A dermoscopic photograph of a skin lesion: 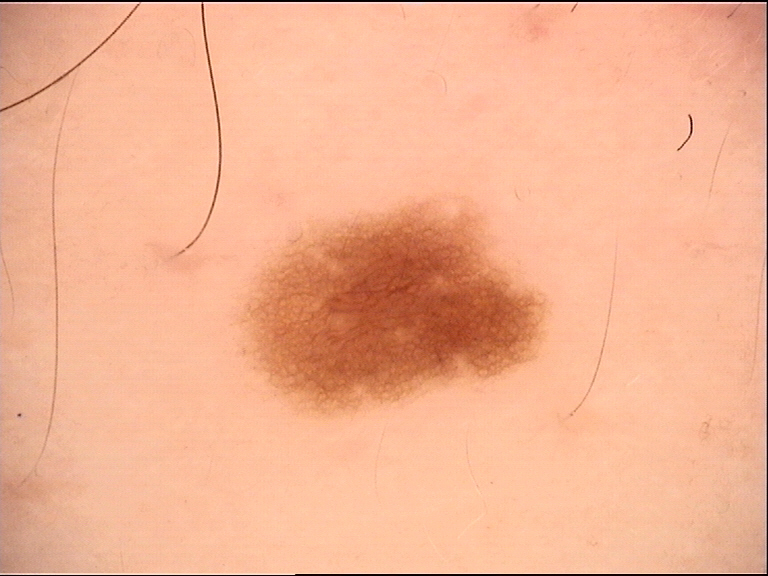The diagnosis was a dysplastic junctional nevus.